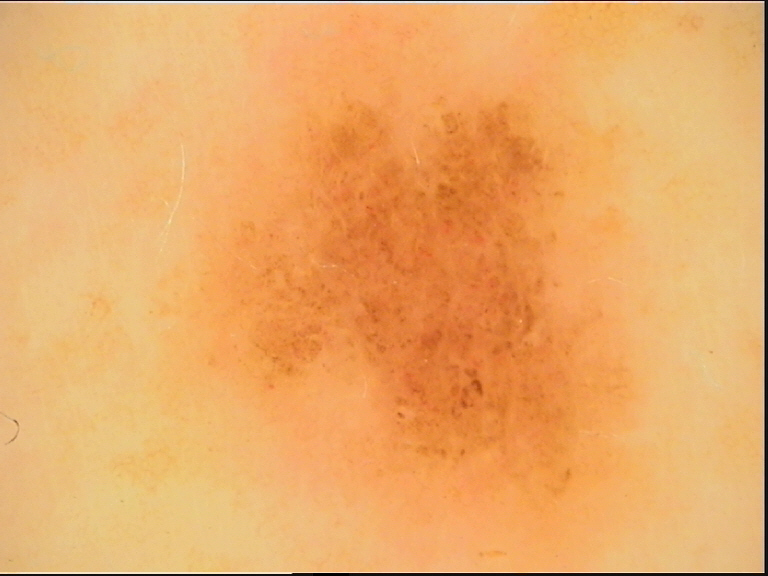{"diagnosis": {"name": "dysplastic junctional nevus", "code": "jd", "malignancy": "benign", "super_class": "melanocytic", "confirmation": "expert consensus"}}